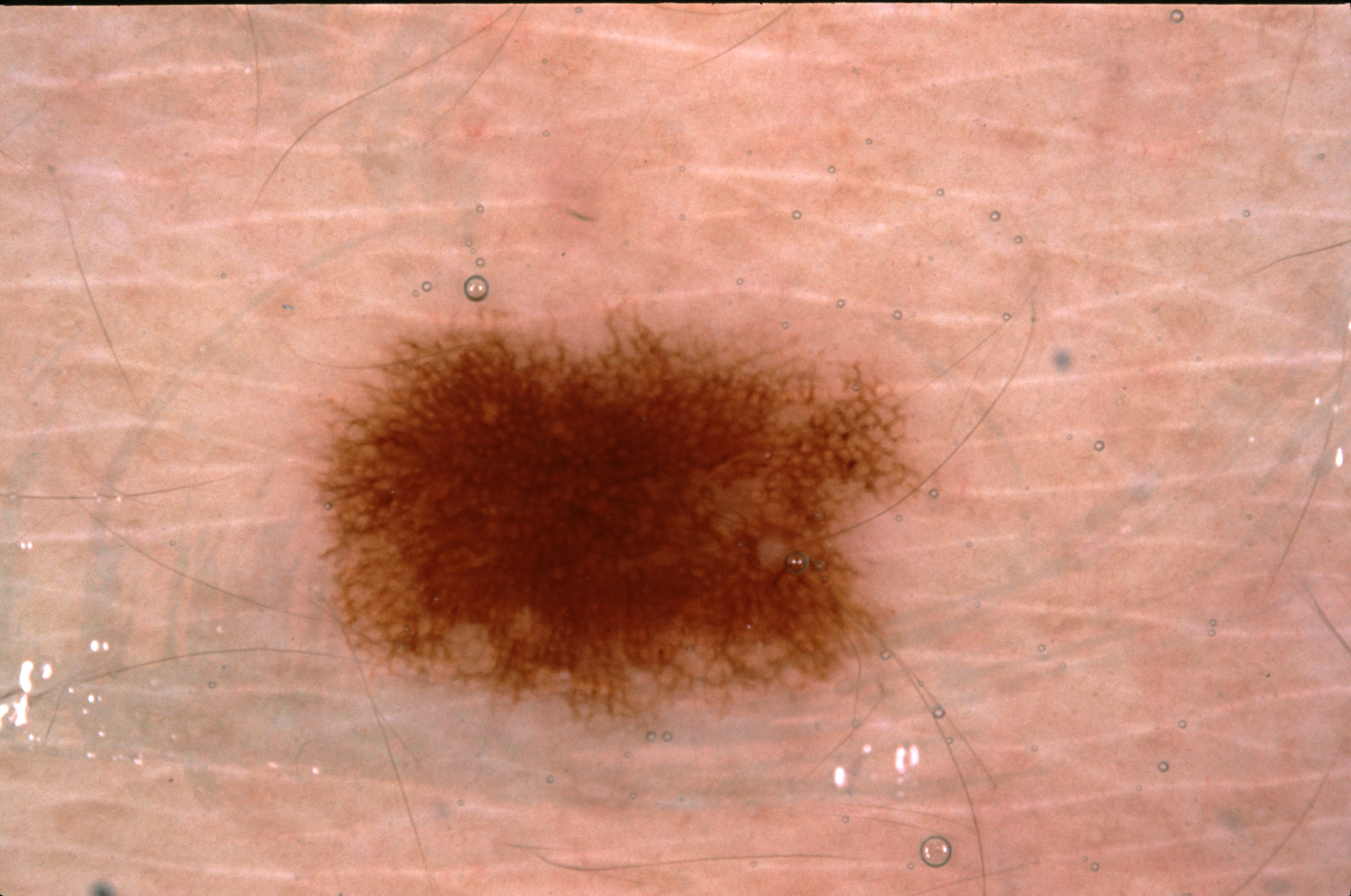A dermoscopic view of a skin lesion.
A male subject, aged around 25.
Dermoscopic assessment notes pigment network, with no negative network, milia-like cysts, or streaks.
As (left, top, right, bottom), the lesion is bounded by bbox=[309, 304, 943, 743].
The diagnostic assessment was a melanocytic nevus, a benign skin lesion.